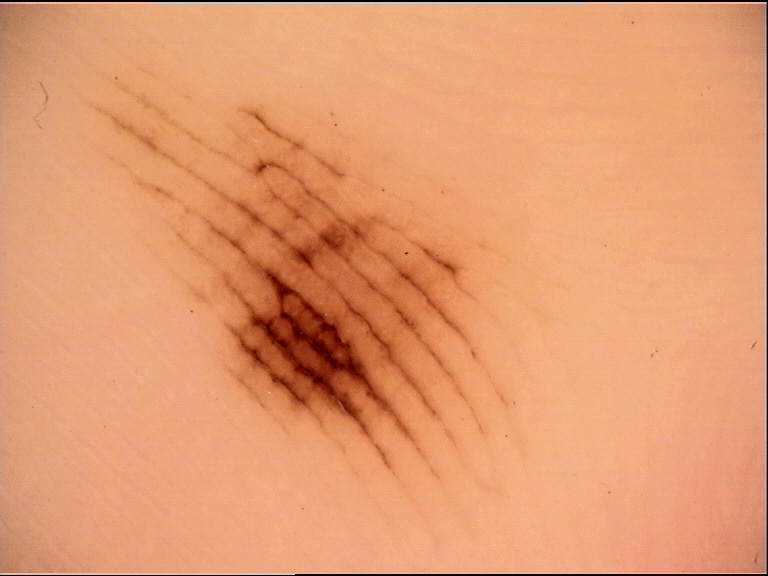Diagnosed as an acral junctional nevus.